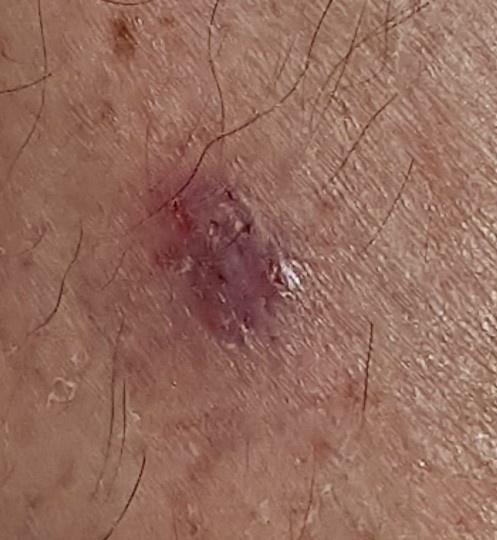patient: male, roughly 70 years of age
modality: clinical photograph
skin phototype: II
diagnostic label: Squamous cell carcinoma (biopsy-proven)